The lesion involves the front of the torso, head or neck, back of the torso and arm. No constitutional symptoms were reported. The photograph was taken at an angle. Present for one to four weeks. Texture is reported as raised or bumpy. The lesion is associated with burning, itching, bothersome appearance and enlargement.
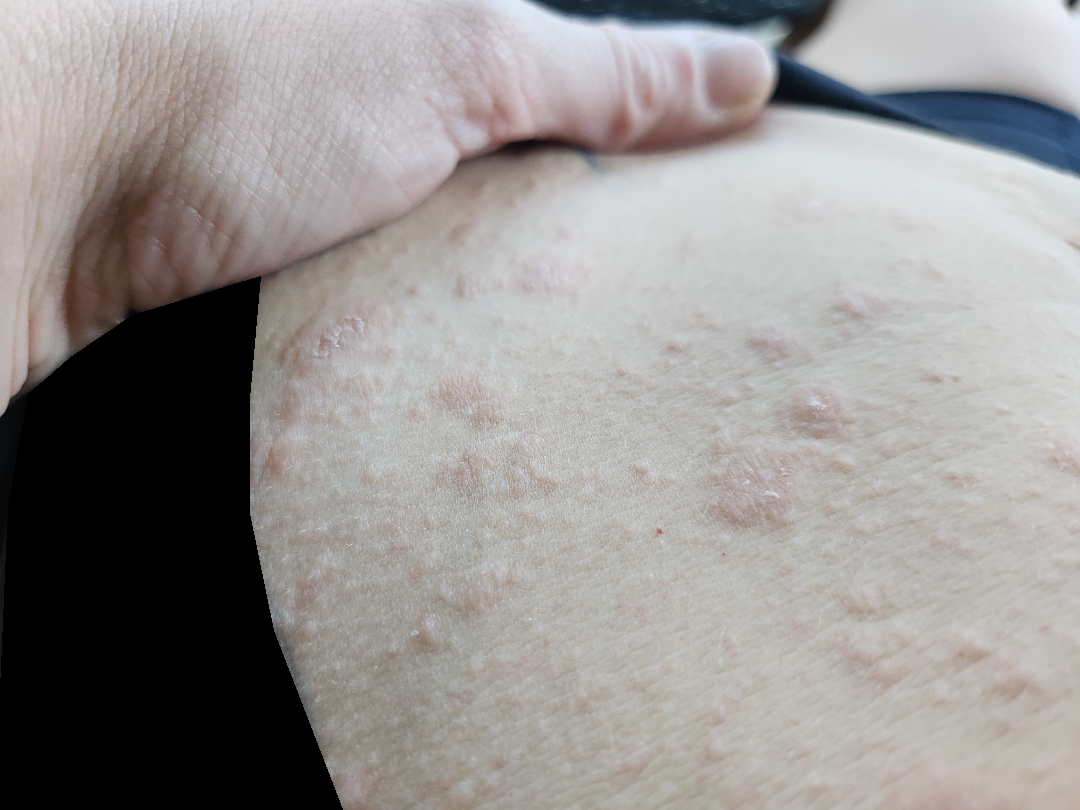| key | value |
|---|---|
| assessment | indeterminate |